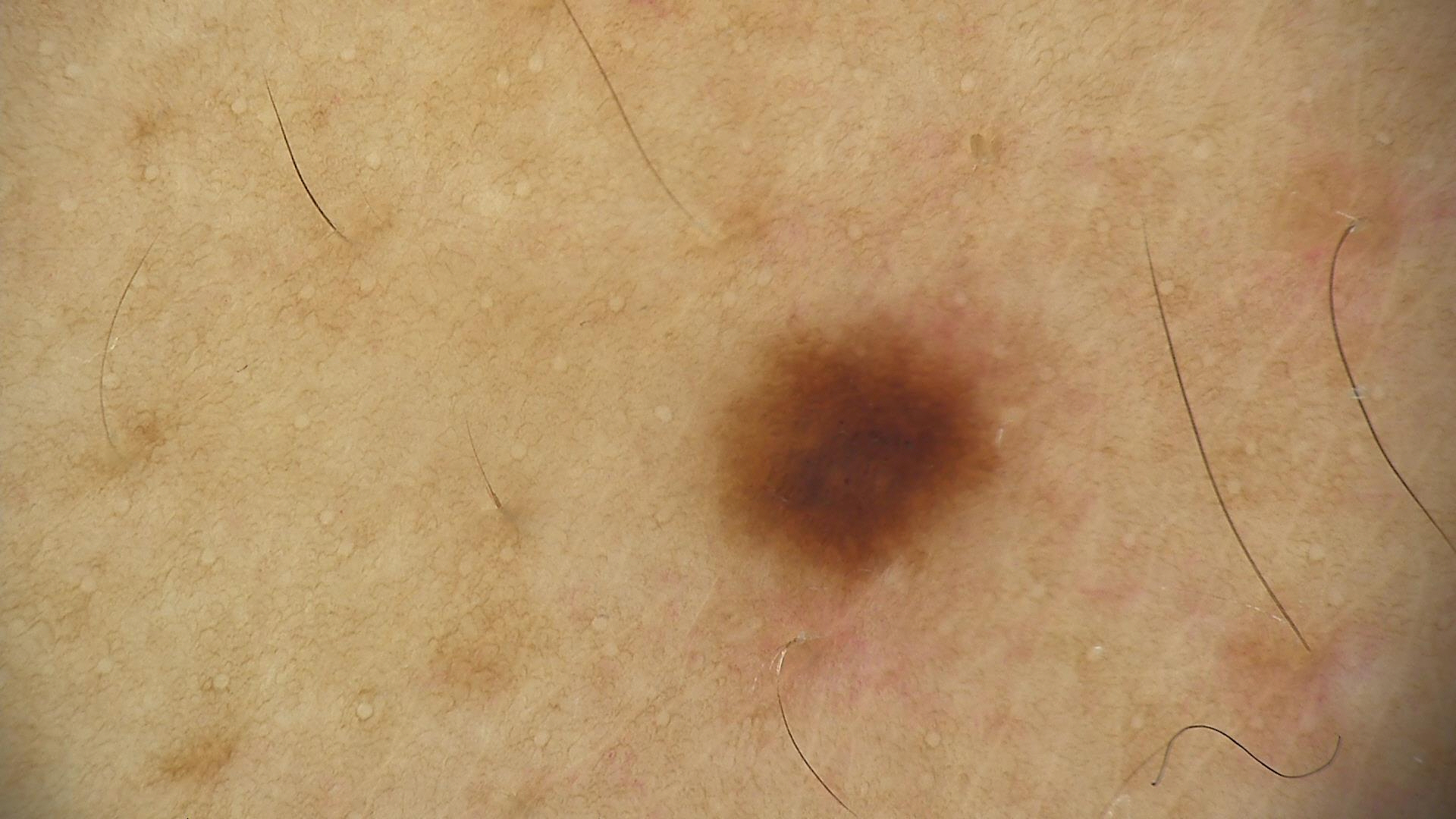A dermatoscopic image of a skin lesion. Labeled as a banal lesion — a junctional nevus.